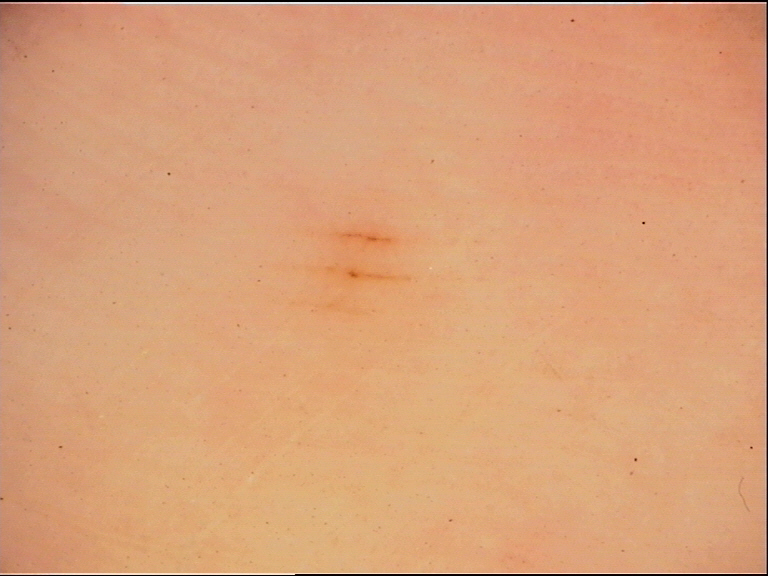Dermoscopy of a skin lesion. This is a banal lesion. The diagnosis was an acral junctional nevus.